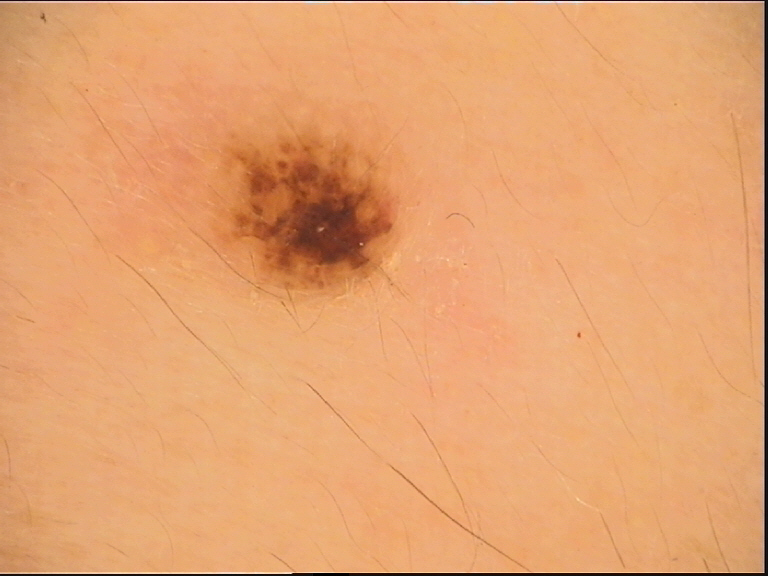A dermoscopy image of a single skin lesion. The diagnosis was a banal lesion — a compound nevus.